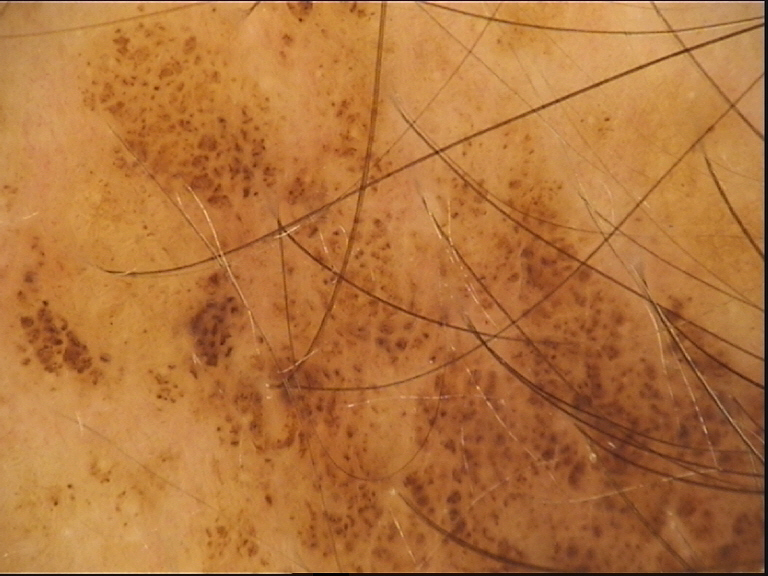Q: What is the diagnosis?
A: congenital junctional nevus (expert consensus)